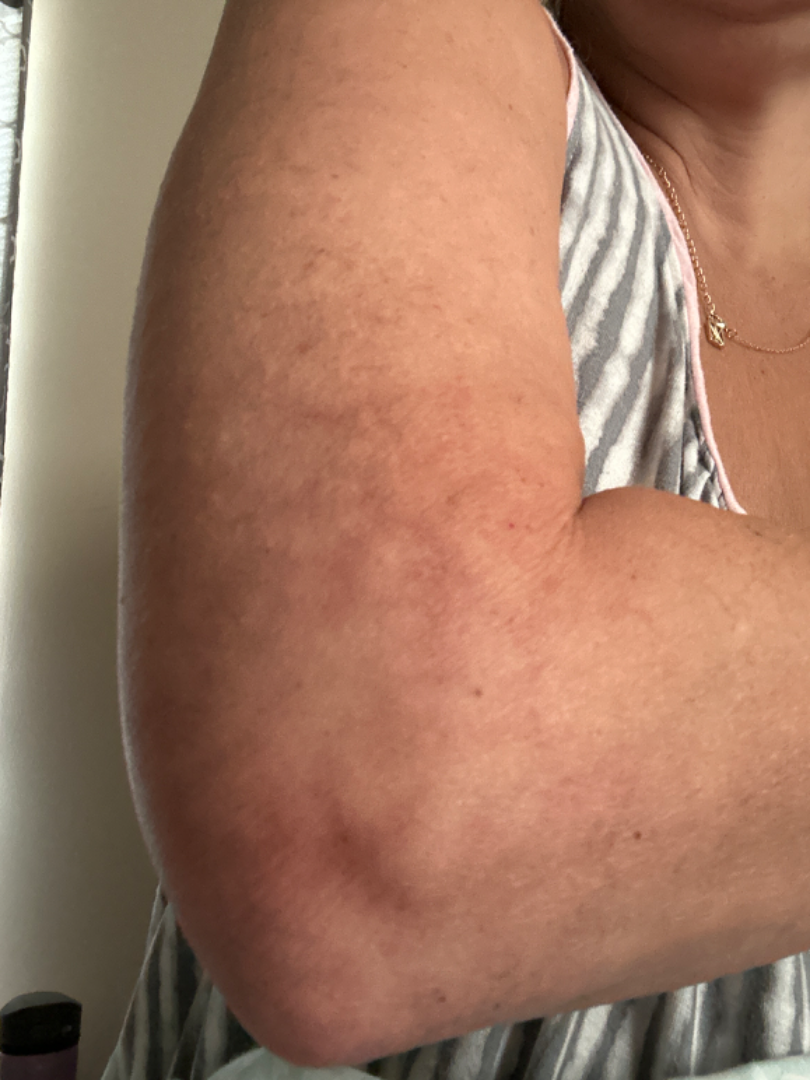present for = one to four weeks
skin tone = Fitzpatrick skin type IV; lay reviewers estimated Monk skin tone scale 3 (US pool) or 2 (India pool)
location = arm
shot type = at an angle
impression = single-reviewer assessment: most consistent with Erythema ab igne